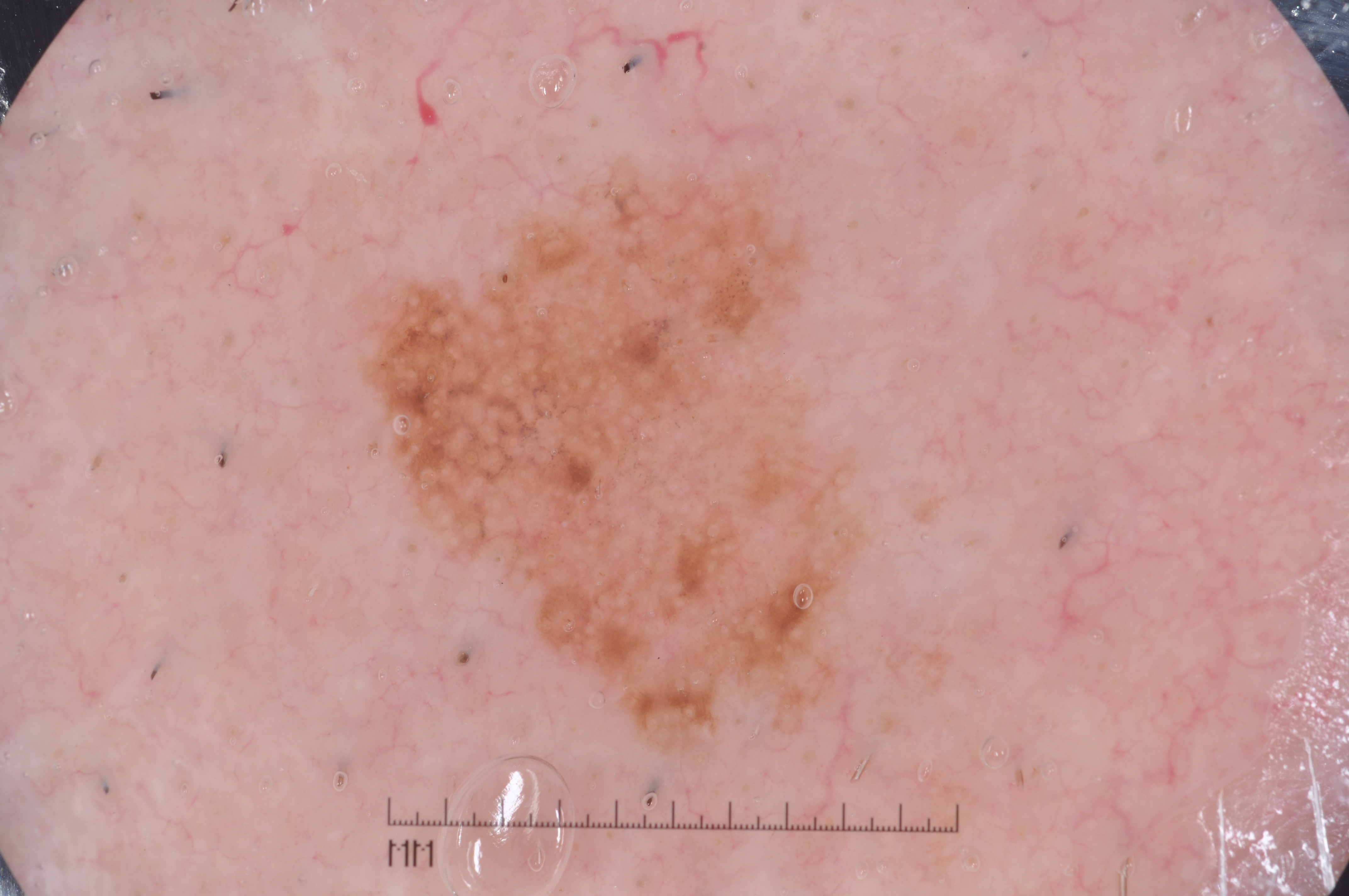Case summary:
A skin lesion imaged with a dermatoscope. The lesion occupies the region [369, 175, 854, 735].
Diagnosis:
Histopathology confirmed a melanoma, a malignant lesion.